A skin lesion imaged with contact-polarized dermoscopy · a female patient about 35 years old · the patient was assessed as Fitzpatrick II.
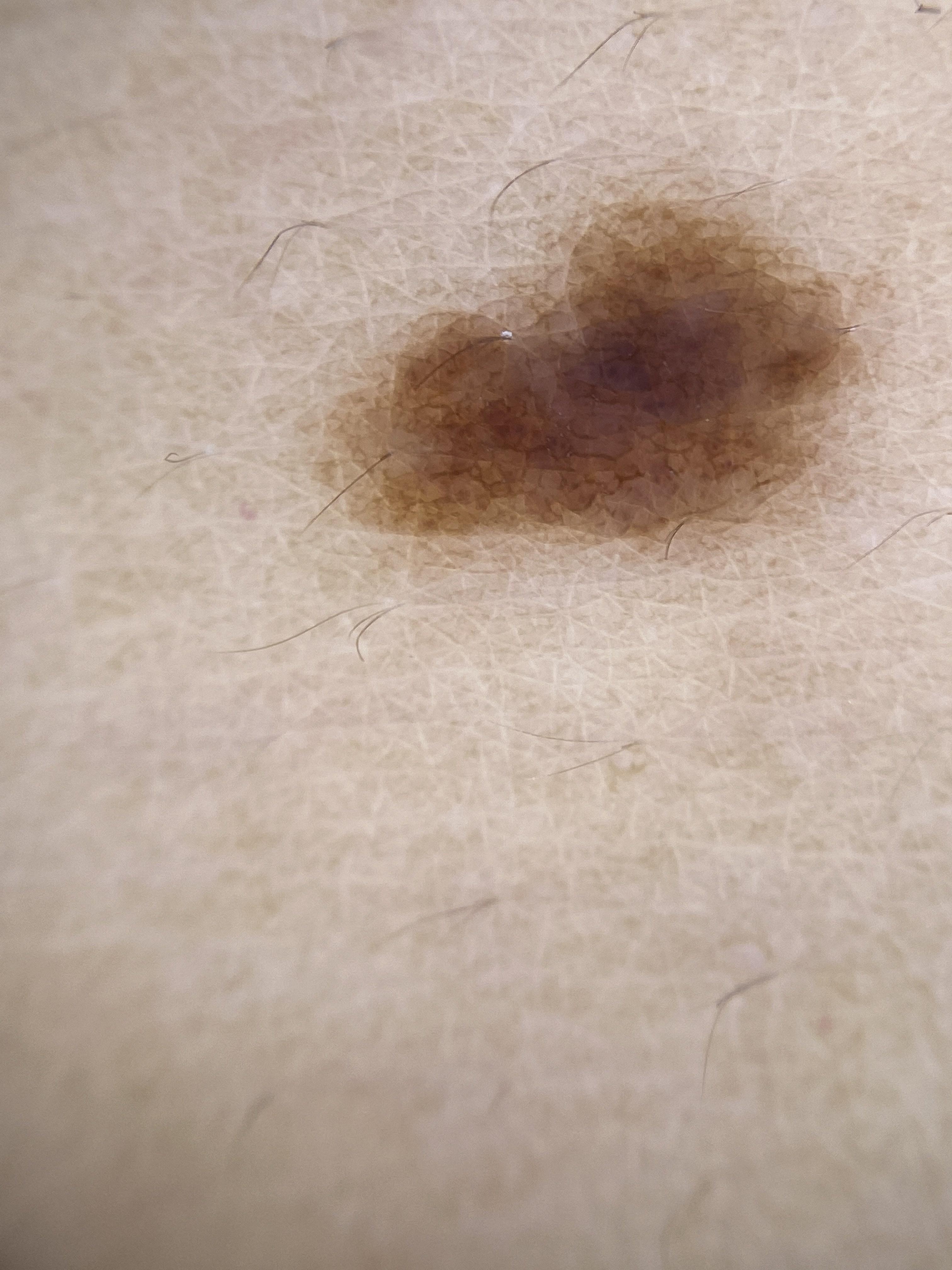The lesion is located on the anterior trunk.
Consistent with a benign lesion — a nevus.